The photograph is a close-up of the affected area. Female contributor, age 60–69. The top or side of the foot and leg are involved.
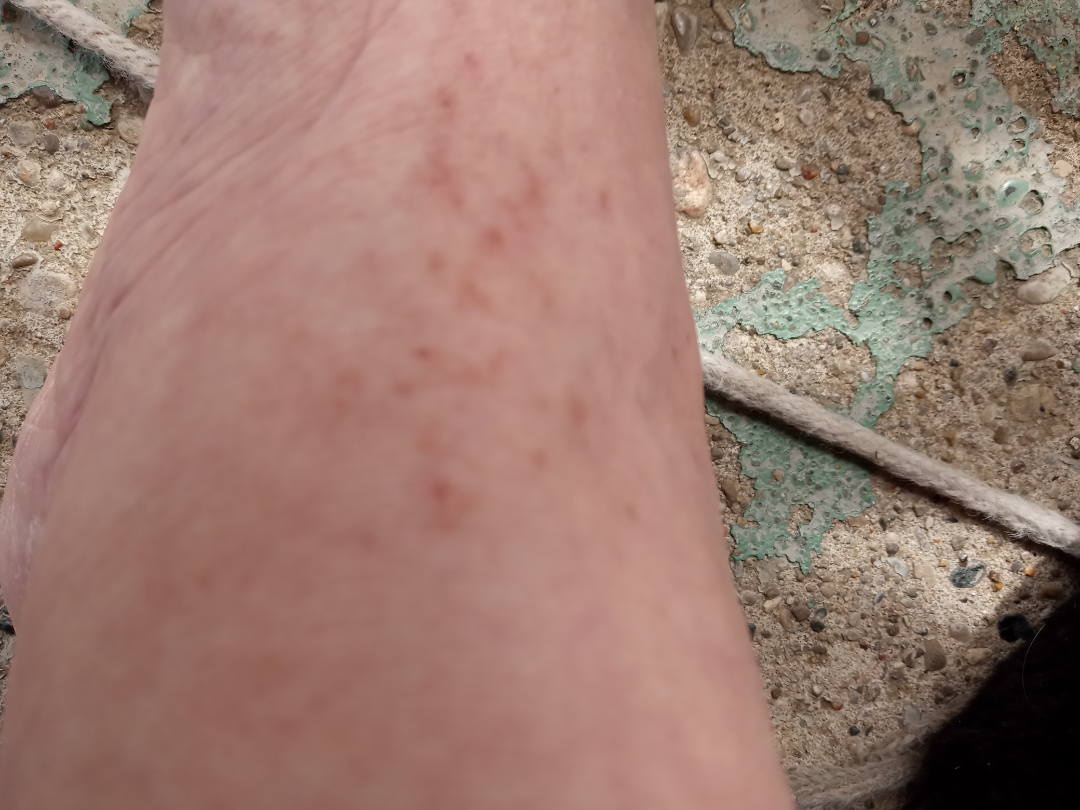differential diagnosis=reviewed remotely by three dermatologists: the impression was split between Scabies and Acute dermatitis, NOS.